This image was taken at an angle.
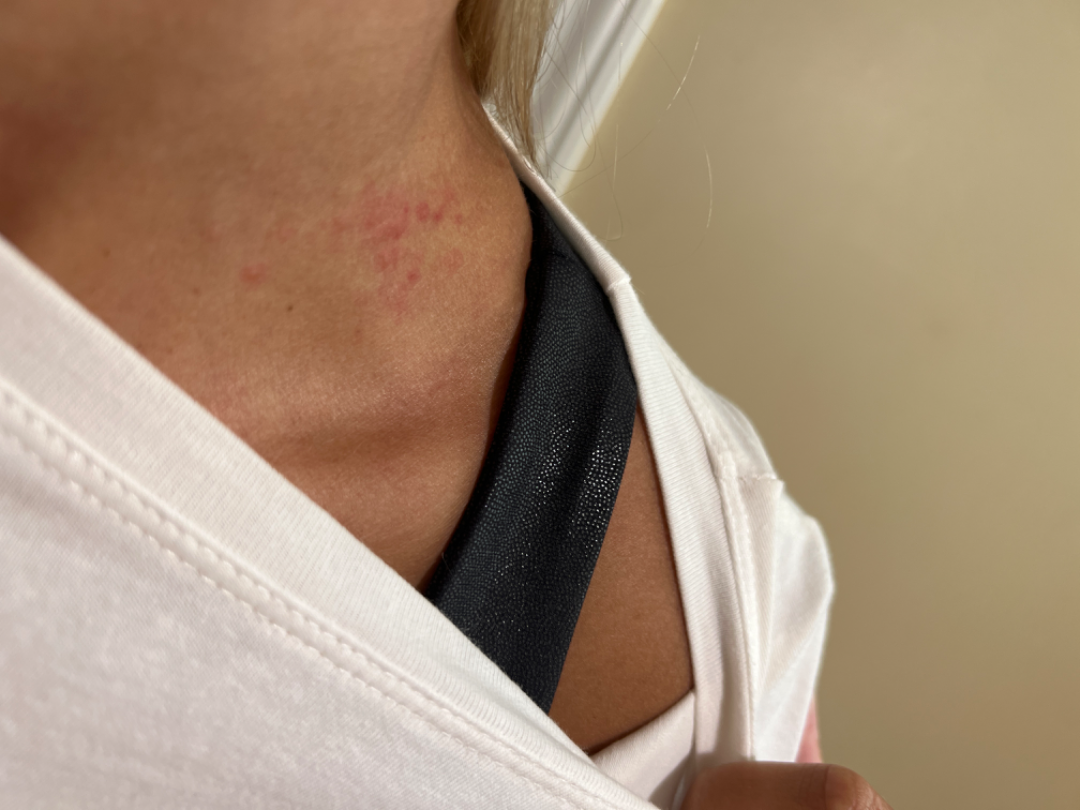differential = Irritant Contact Dermatitis (100%).